Self-categorized by the patient as a rash · female contributor, age 18–29 · located on the arm · the lesion is associated with itching and burning · reported duration is one to four weeks · texture is reported as rough or flaky · the photograph is a close-up of the affected area · no constitutional symptoms were reported.
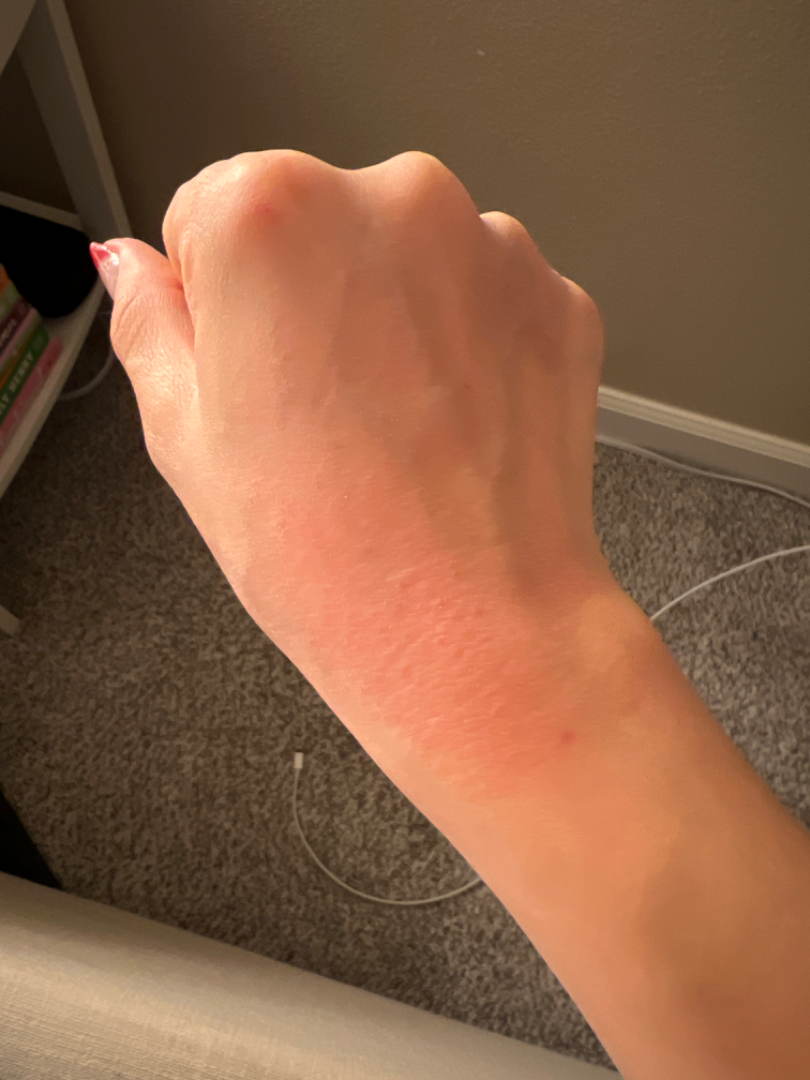The impression on review was Acute dermatitis, NOS.